A close-up photograph · skin tone: Fitzpatrick skin type V; human graders estimated Monk skin tone scale 4 or 5:
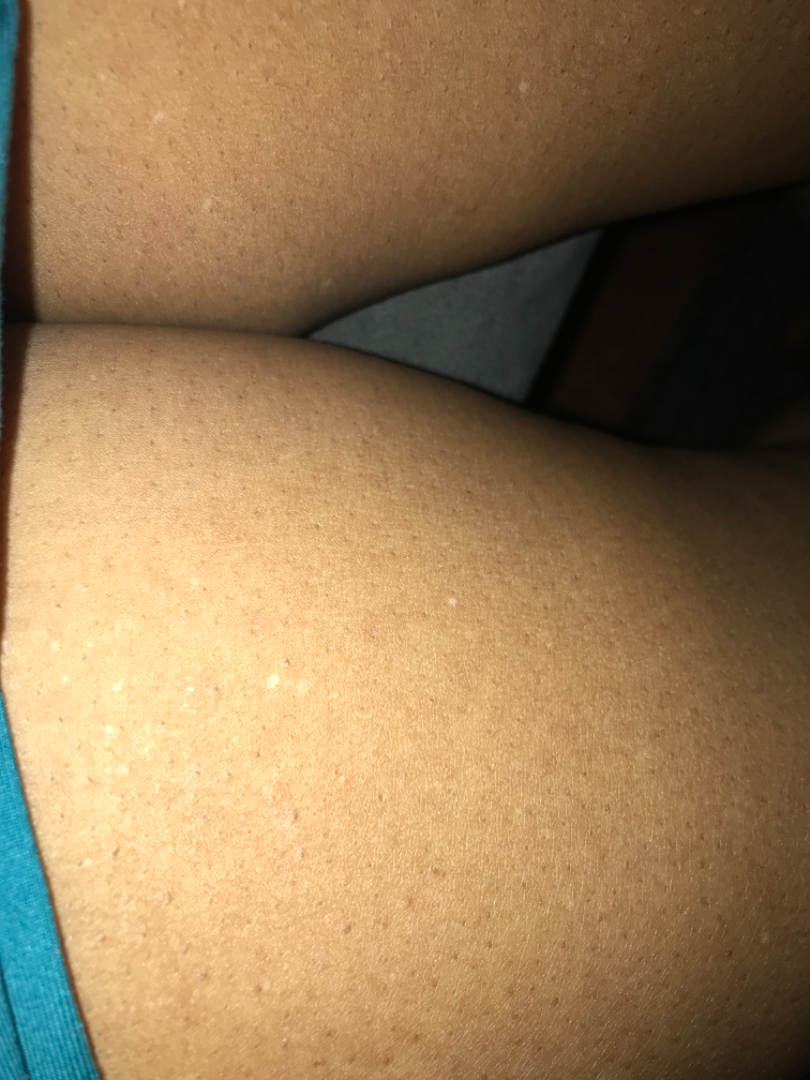Review: The skin findings could not be characterized from the image.